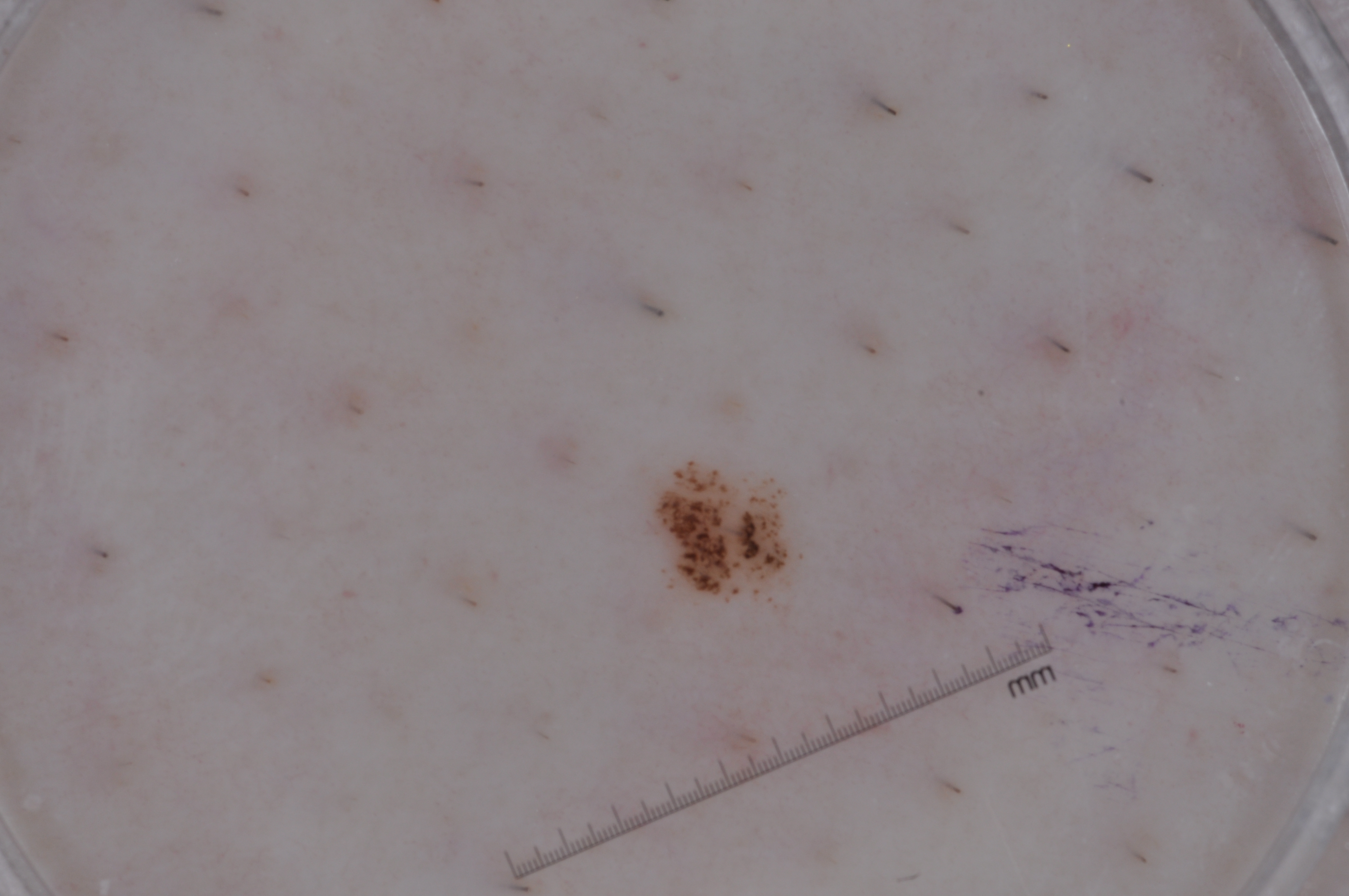<dermoscopy>
<patient>
  <sex>female</sex>
  <age_approx>55</age_approx>
</patient>
<image>
  <modality>dermoscopy</modality>
</image>
<lesion_extent>small</lesion_extent>
<lesion_location>
  <bbox_xyxy>654, 469, 780, 588</bbox_xyxy>
</lesion_location>
<dermoscopic_features>
  <present/>
  <absent>pigment network, negative network, streaks, milia-like cysts</absent>
</dermoscopic_features>
<diagnosis>
  <name>melanoma</name>
  <malignancy>malignant</malignancy>
  <lineage>melanocytic</lineage>
  <provenance>histopathology</provenance>
</diagnosis>
</dermoscopy>